A dermatoscopic image of a skin lesion.
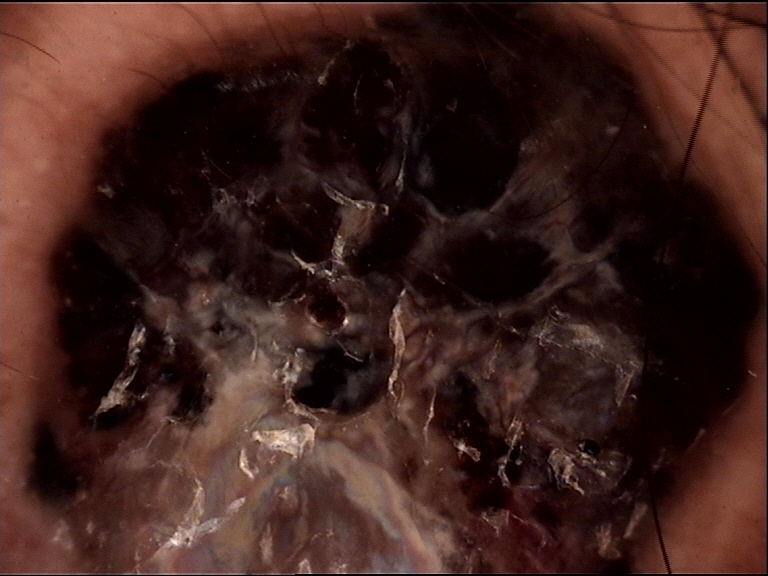{"diagnosis": {"name": "melanoma", "code": "mel", "malignancy": "malignant", "super_class": "melanocytic", "confirmation": "histopathology"}}